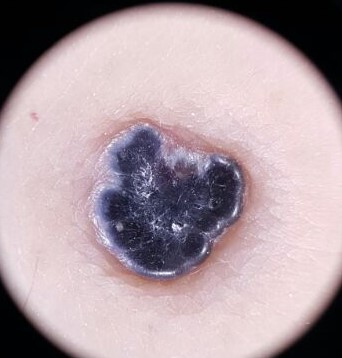* image type · dermoscopy
* classification · vascular
* diagnostic label · angiokeratoma (expert consensus)